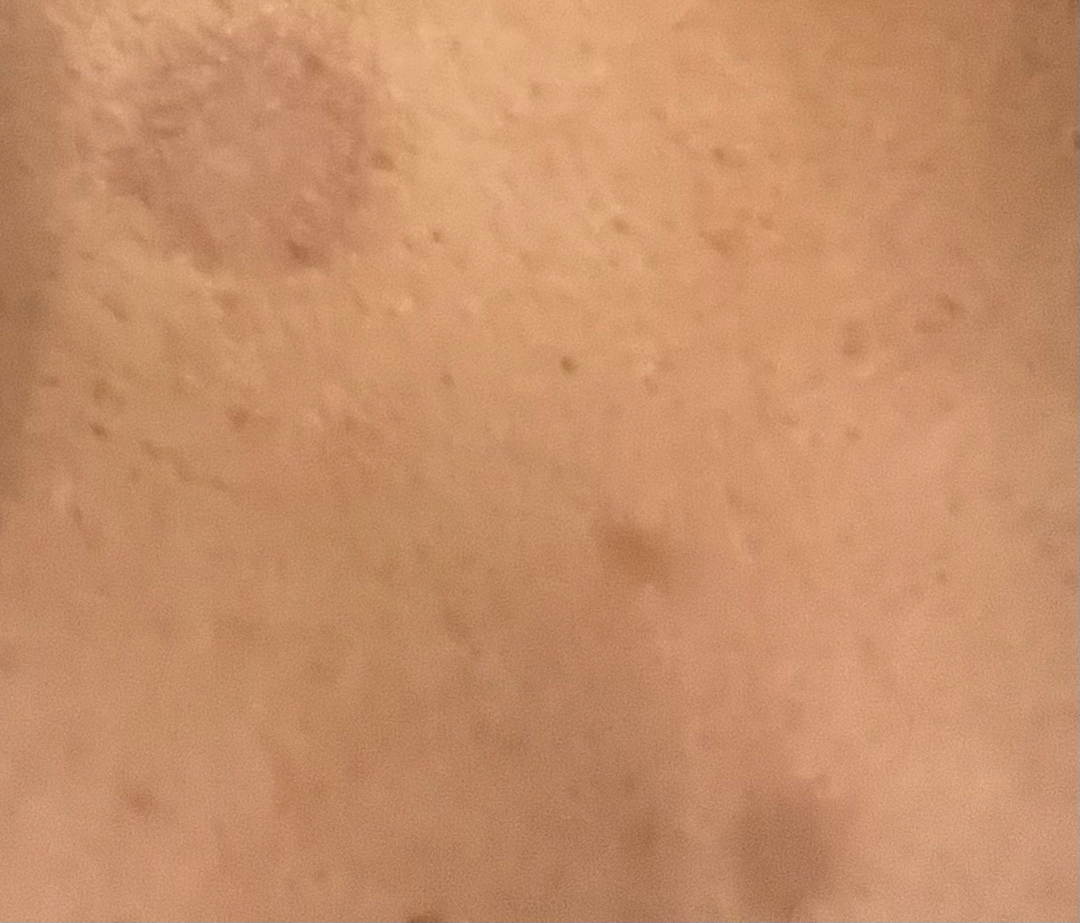• assessment — indeterminate